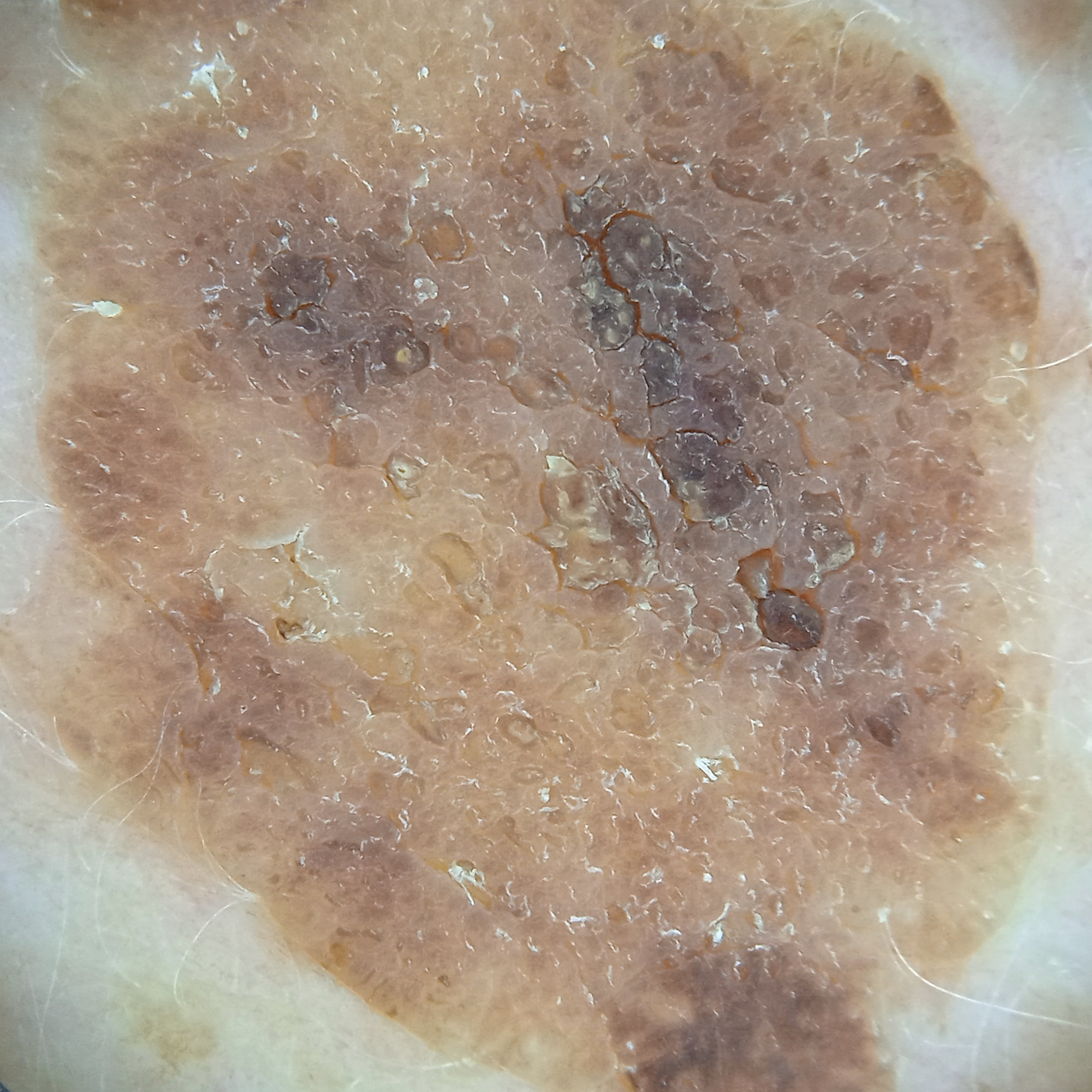The patient says their skin tans without first burning. On a questionnaire the patient reported no immunosuppression. A female subject 78 years of age. Imaged for a research study, with no referral diagnosis recorded. The lesion is located on the back. The lesion is about 15.7 mm across. Four dermatologists reviewed the lesion; the consensus was a seborrheic keratosis; the reviewers were highly confident.